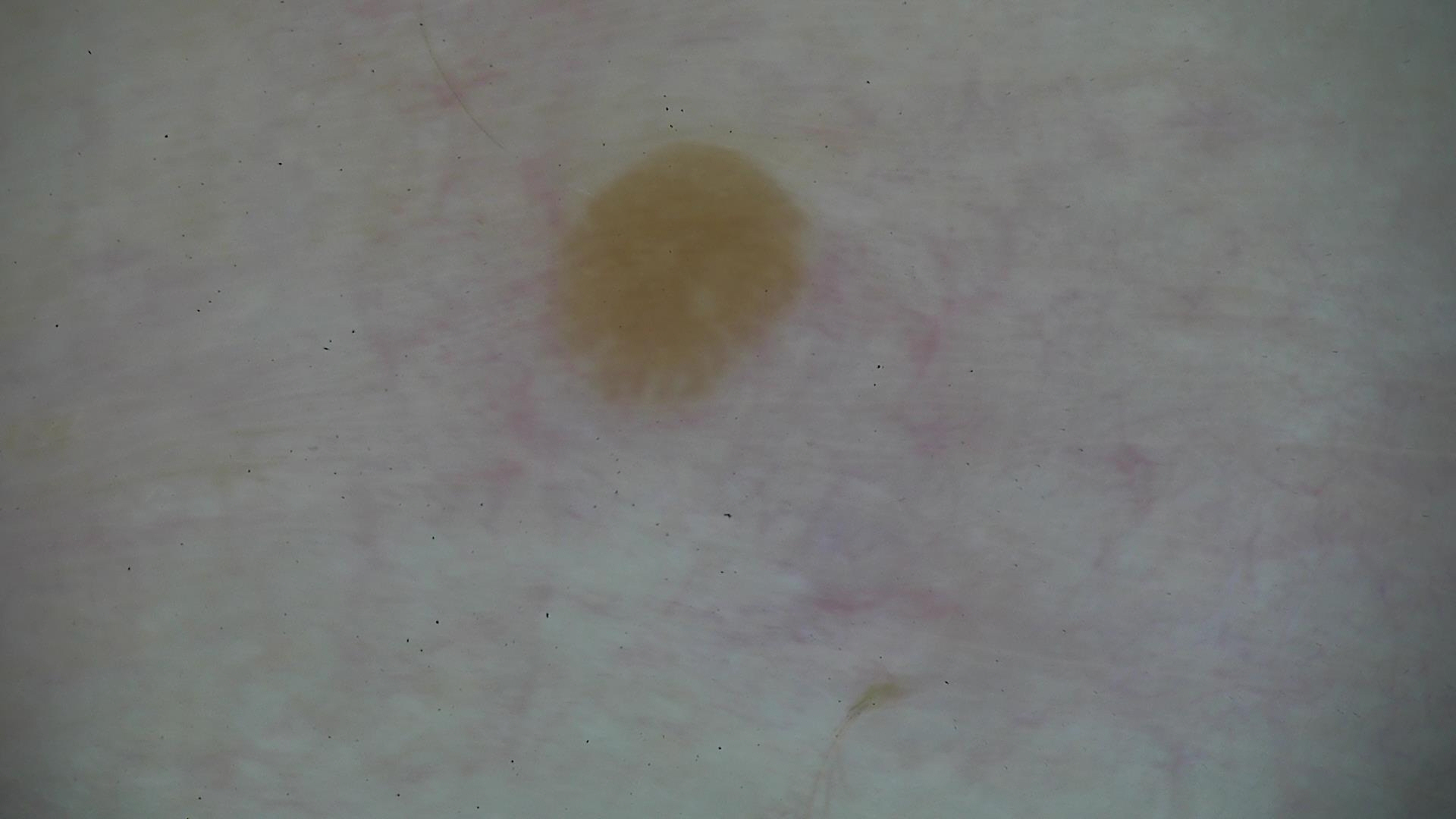A dermoscopic image of a skin lesion. This is a keratinocytic lesion. Consistent with a seborrheic keratosis.